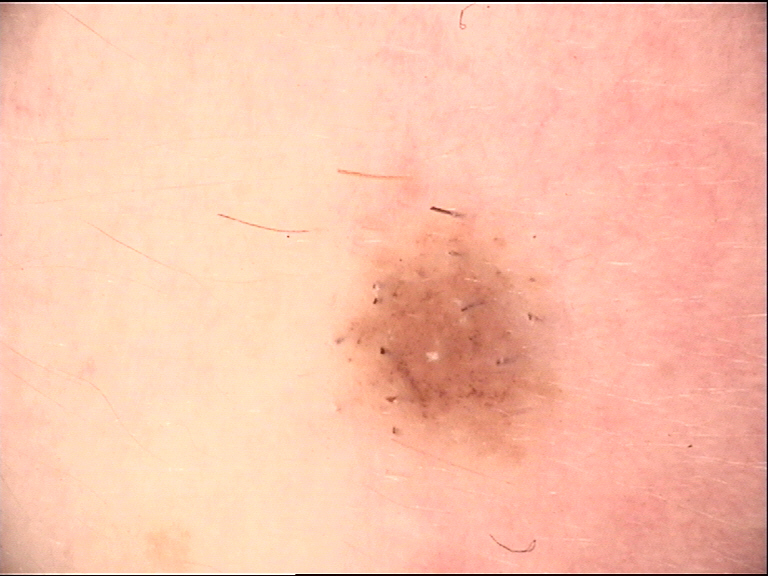Impression: Classified as a banal lesion — a Miescher nevus.